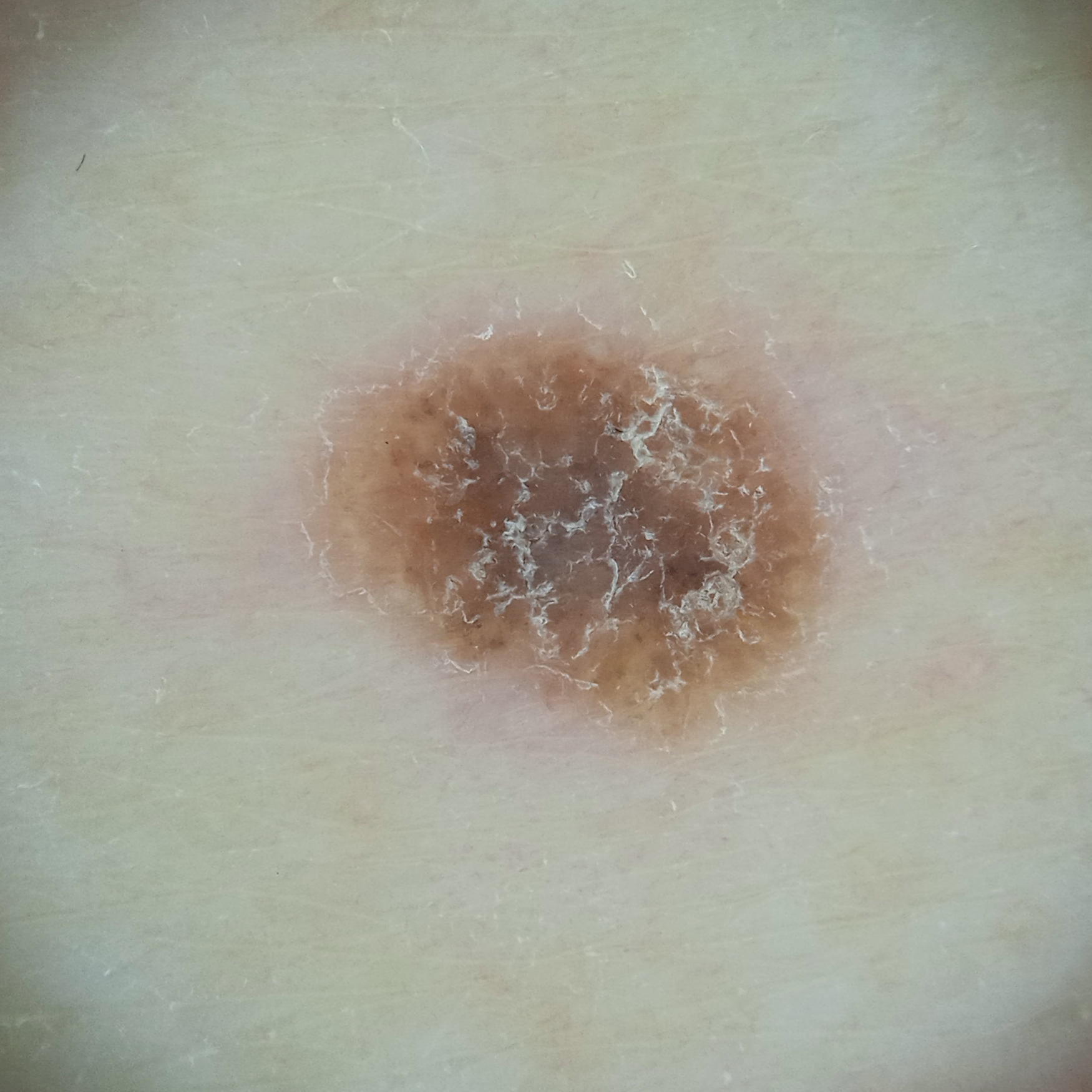diagnosis = seborrheic keratosis (dermatologist consensus).